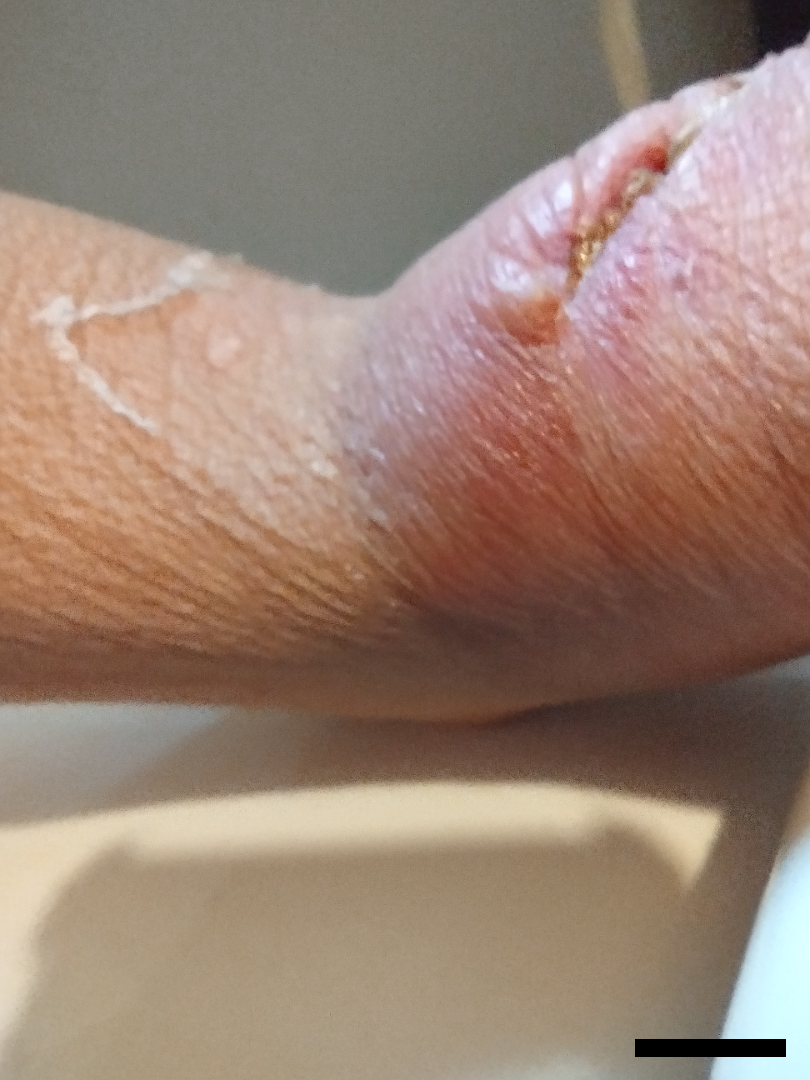The contributor is female. Located on the arm. The photo was captured at an angle. The impression is Local infection of wound.